A male subject 15 years old · a clinical photograph of a skin lesion · the patient says their skin tans without first burning · the patient reports no immunosuppression · imaged for a research study, with no referral diagnosis recorded · the patient describes having few moles overall.
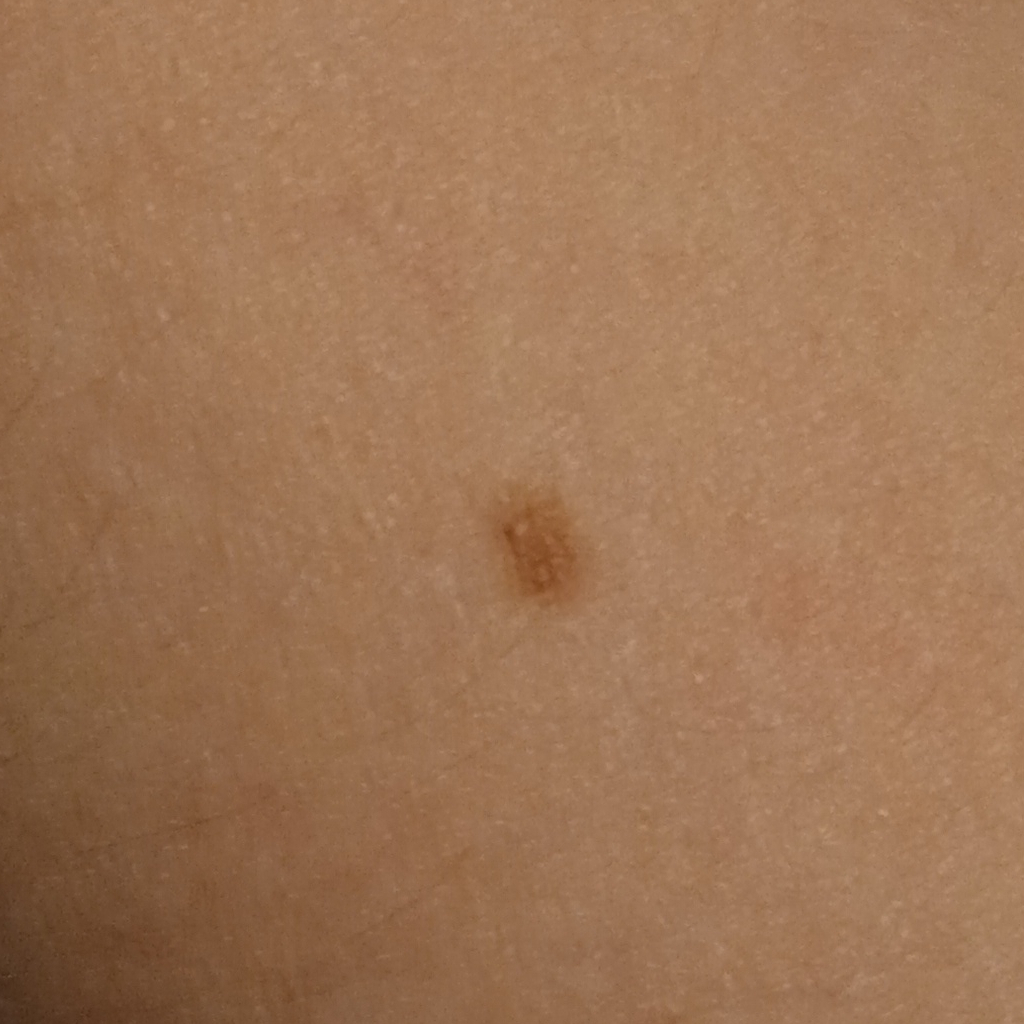Findings:
The lesion involves an arm. Measuring roughly 3.5 mm.
Assessment:
The consensus diagnosis for this lesion was a melanocytic nevus.